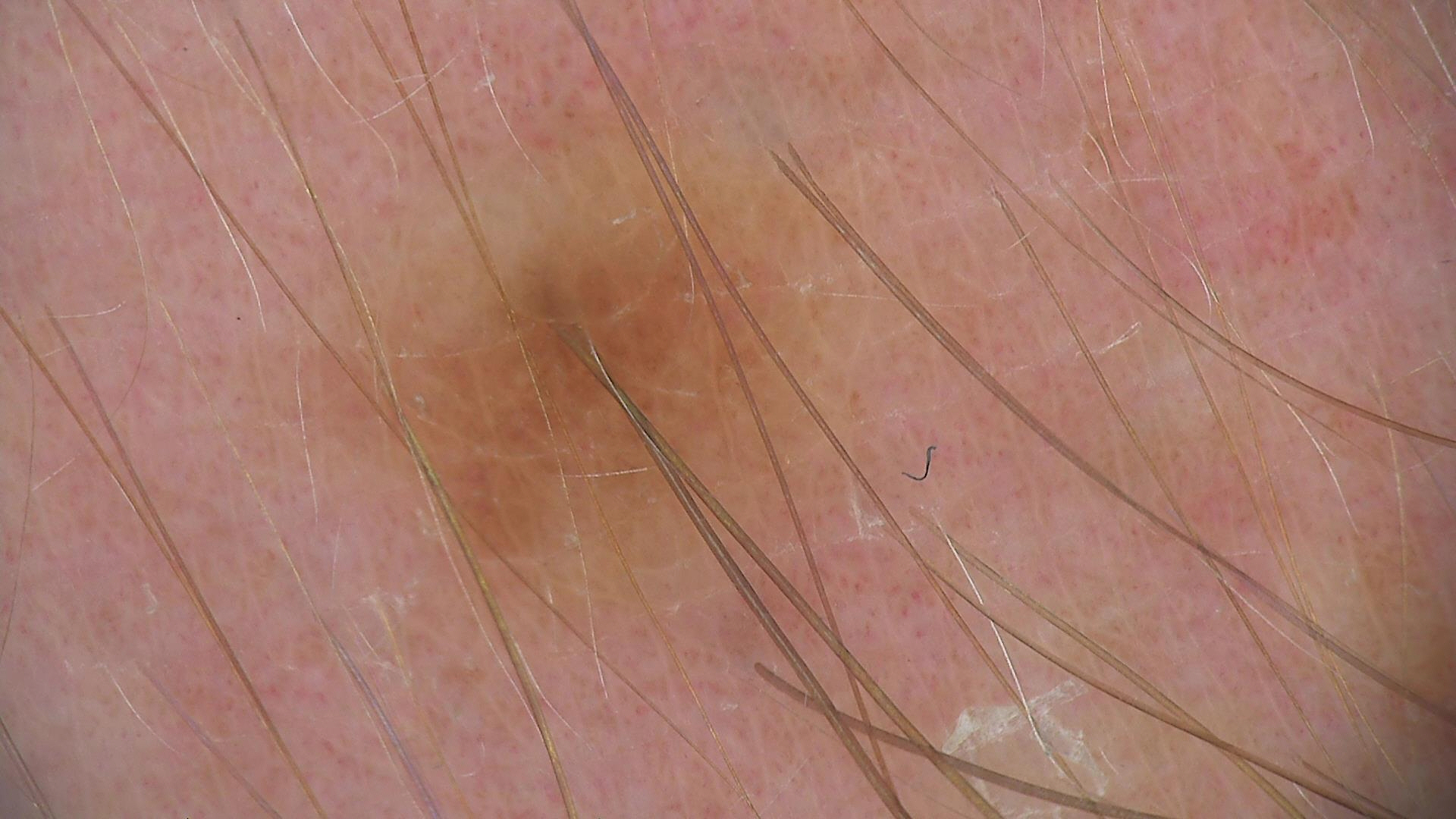diagnostic label: dysplastic junctional nevus (expert consensus).